A dermoscopic photograph of a skin lesion.
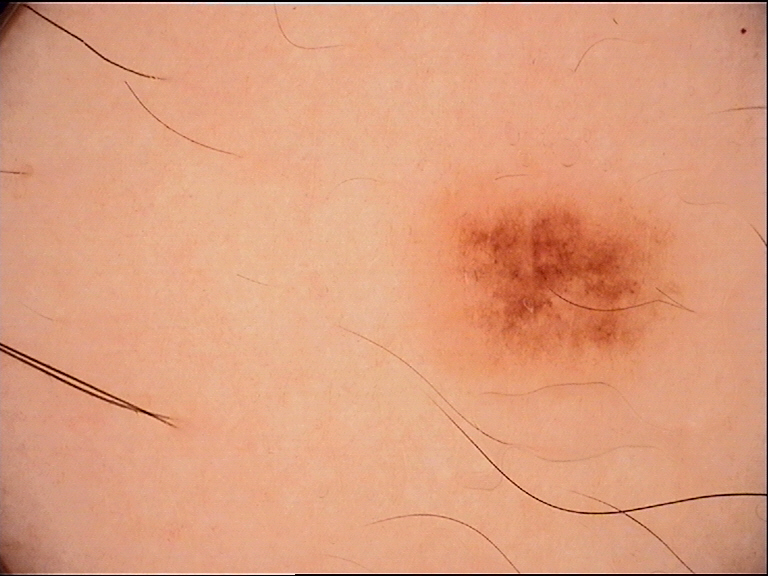Consistent with a dysplastic junctional nevus.